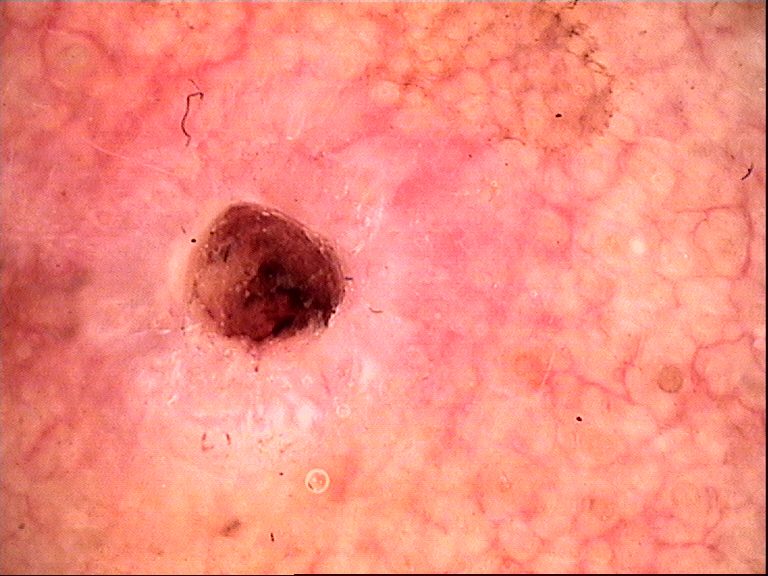A dermoscopic close-up of a skin lesion.
Biopsy-confirmed as a malignant, keratinocytic lesion — a basal cell carcinoma.